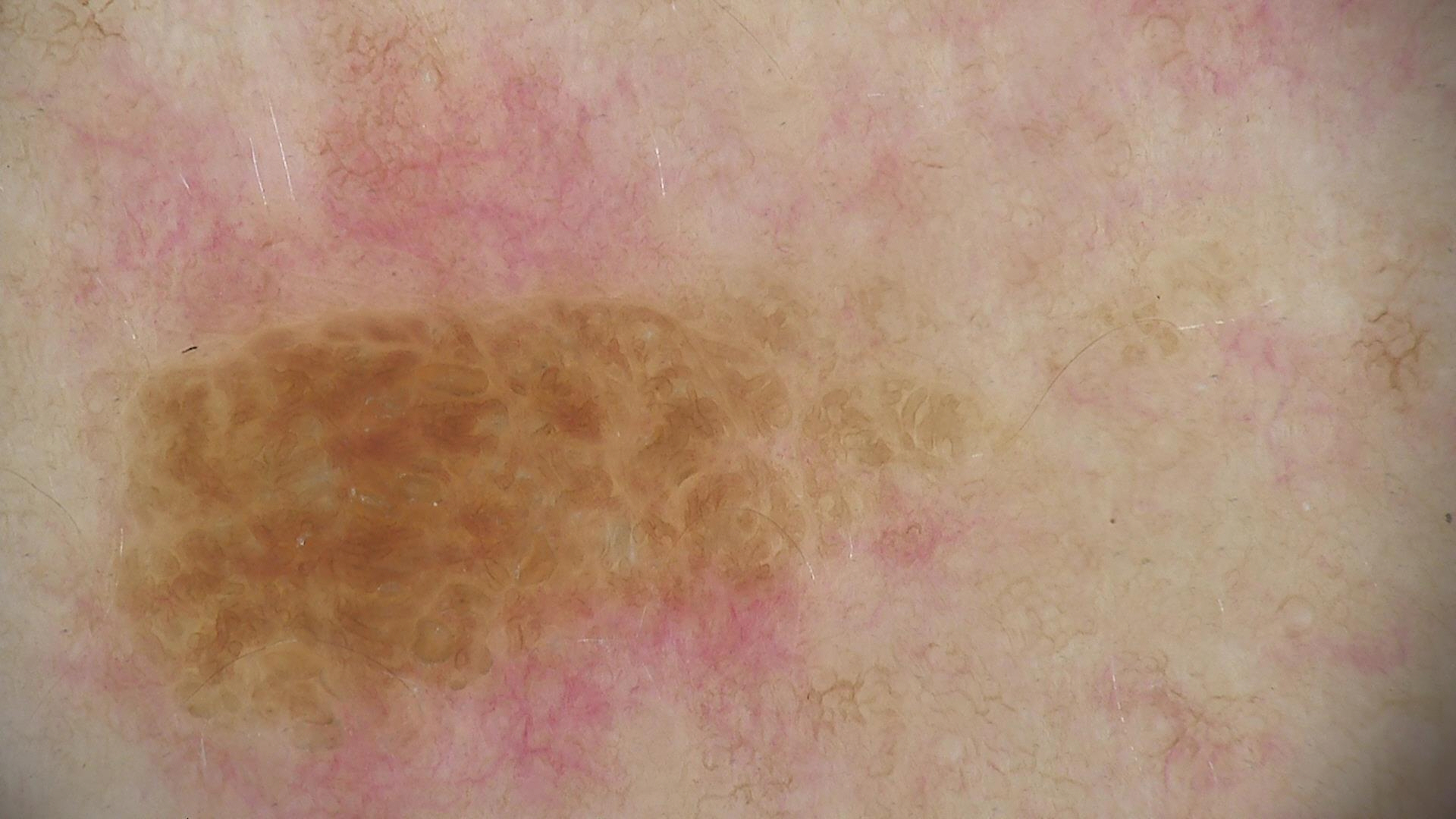class: compound nevus (expert consensus).